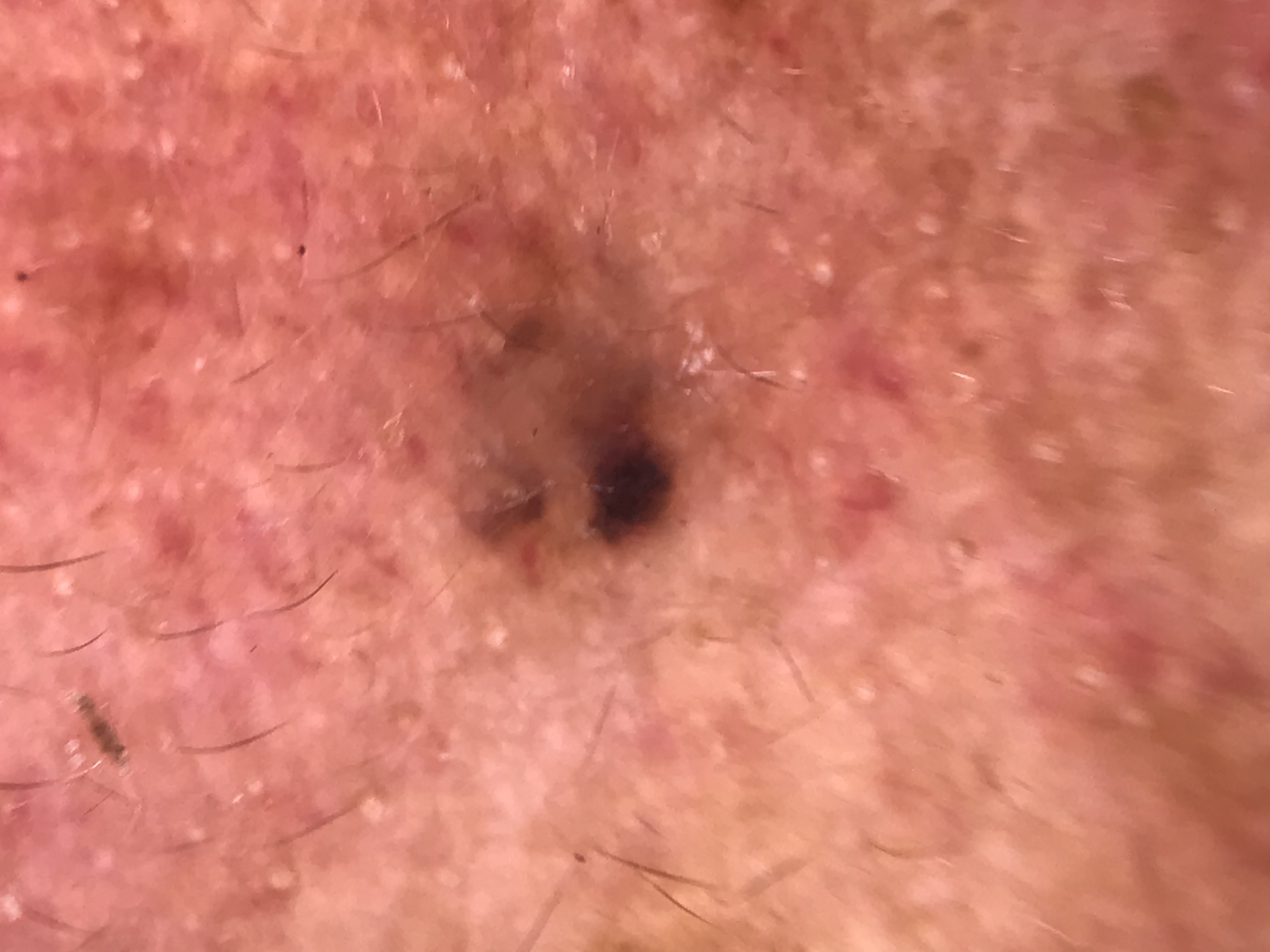This is a keratinocytic lesion.
The biopsy diagnosis was a basal cell carcinoma.